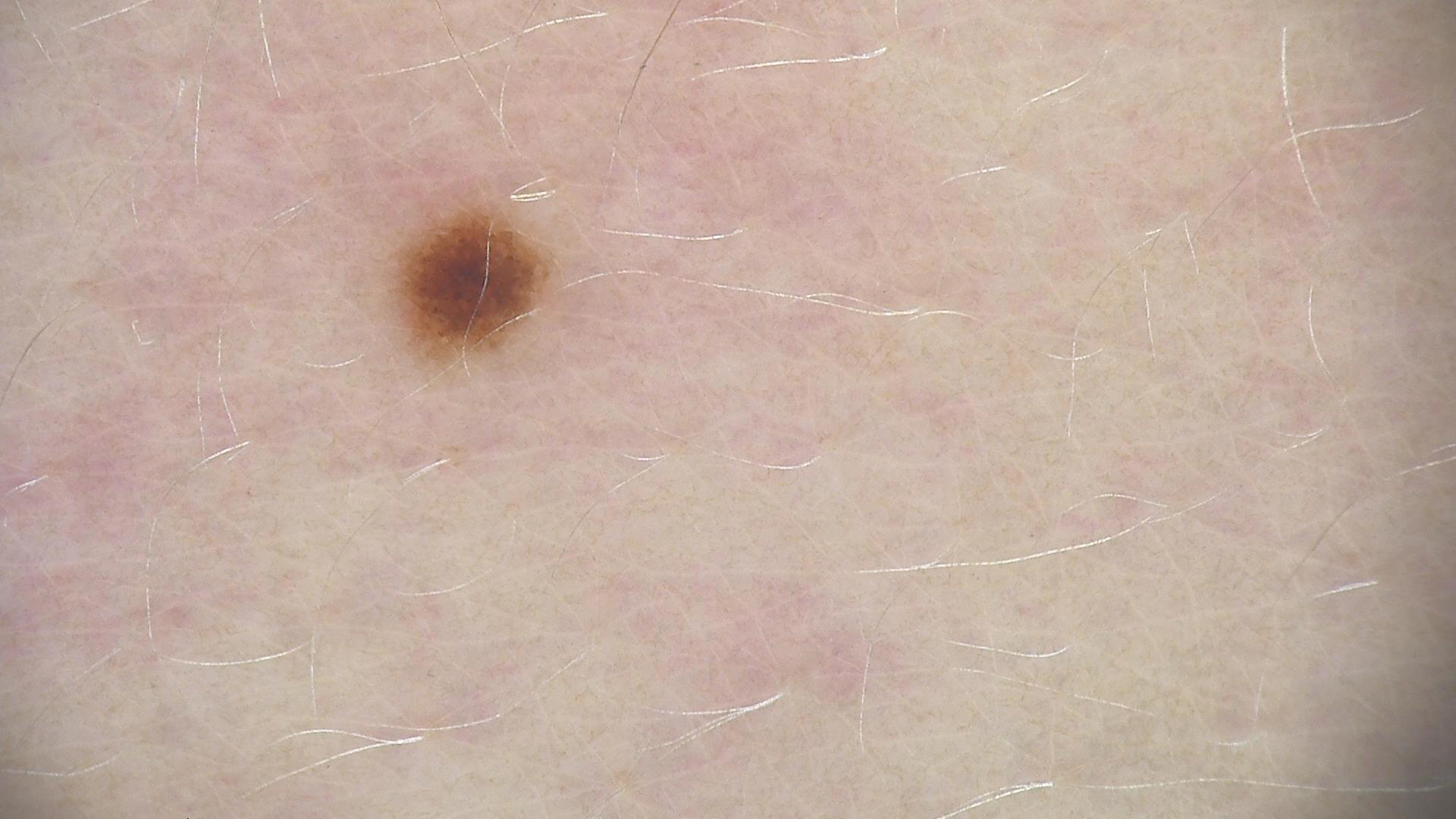image type = dermatoscopy, diagnostic label = dysplastic junctional nevus (expert consensus).